A skin lesion imaged with a dermatoscope; a female patient, about 15 years old — 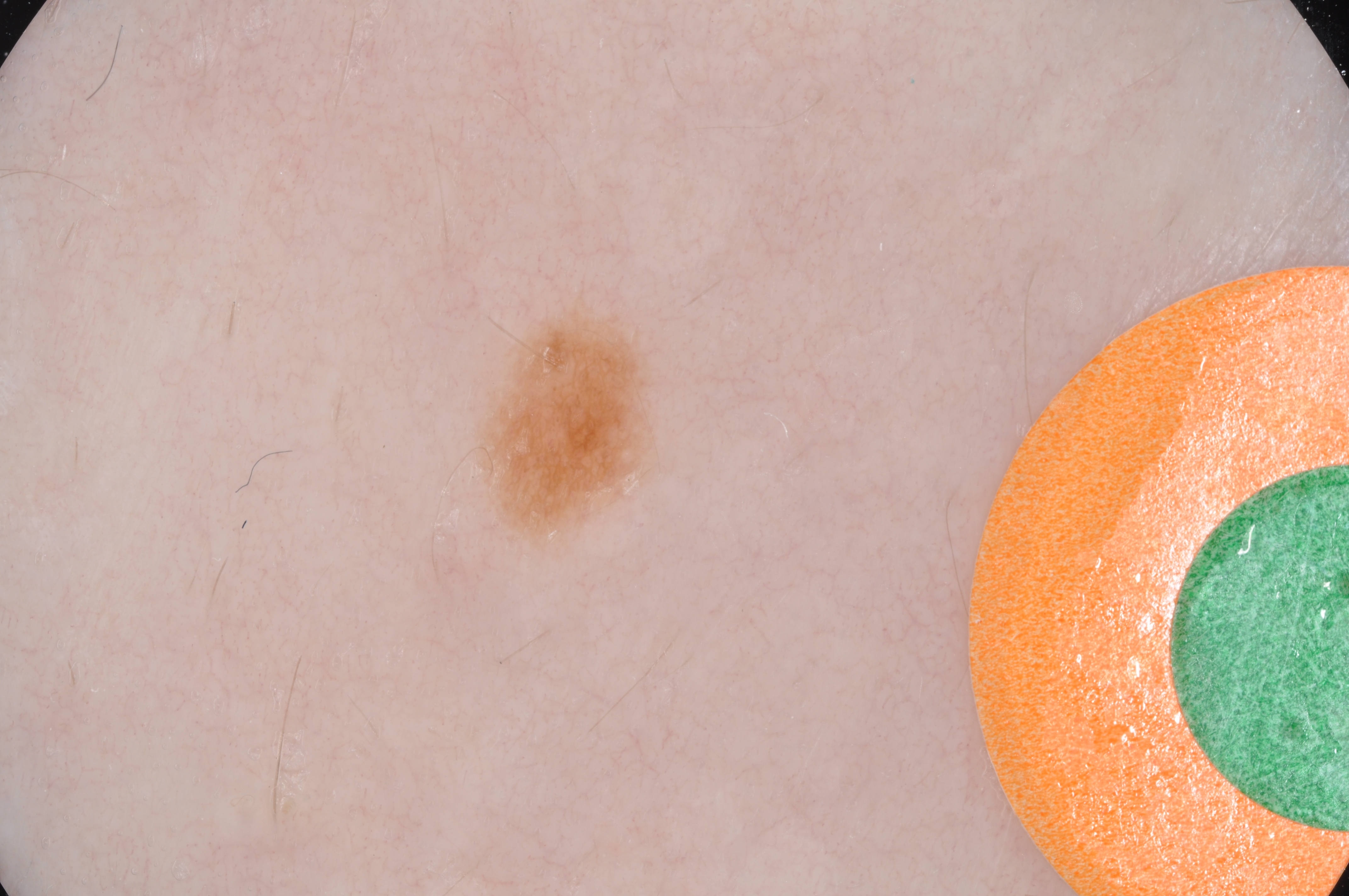extent = small | dermoscopic findings = pigment network; absent: globules, streaks, negative network, and milia-like cysts | bounding box = x1=471, y1=298, x2=665, y2=549 | impression = a melanocytic nevus.